An image taken at an angle. Self-categorized by the patient as a rash. Skin tone: FST II; human graders estimated 1 on the Monk skin tone scale. The patient notes the lesion is raised or bumpy. The arm is involved. The patient is 18–29, female. Present for less than one week: 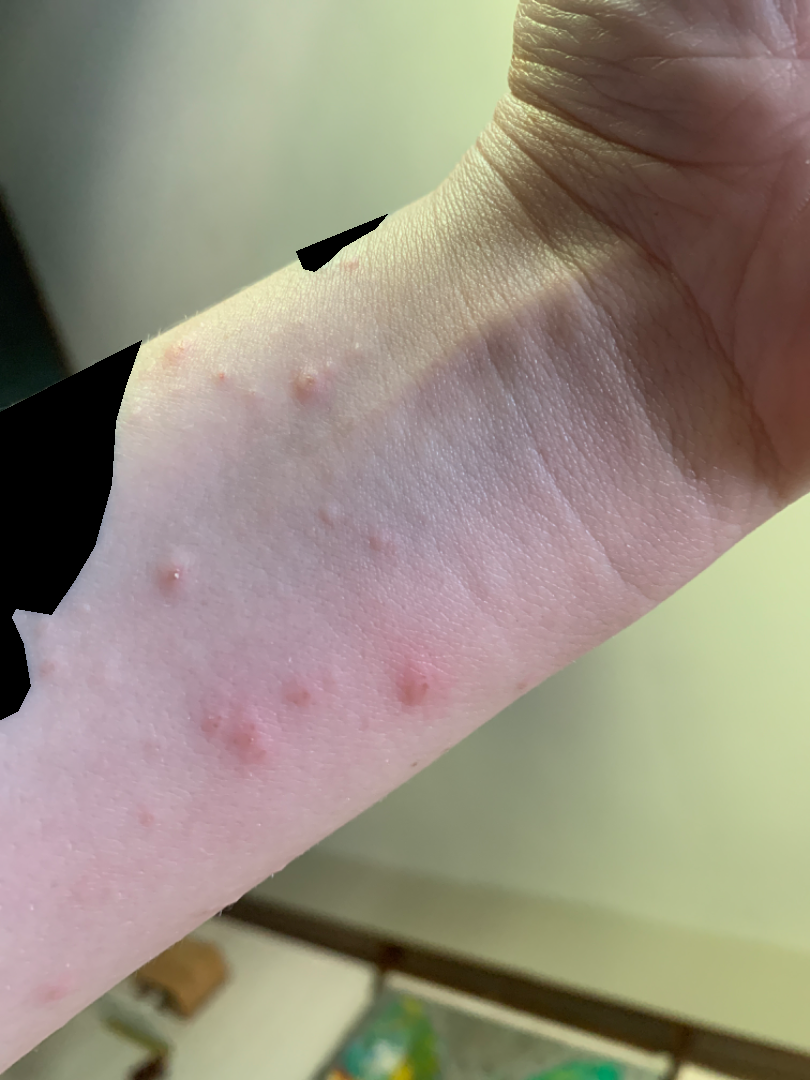Q: What is the differential diagnosis?
A: reviewed remotely by three dermatologists: Scabies and Insect Bite were each considered, in no particular order; less likely is Allergic Contact Dermatitis